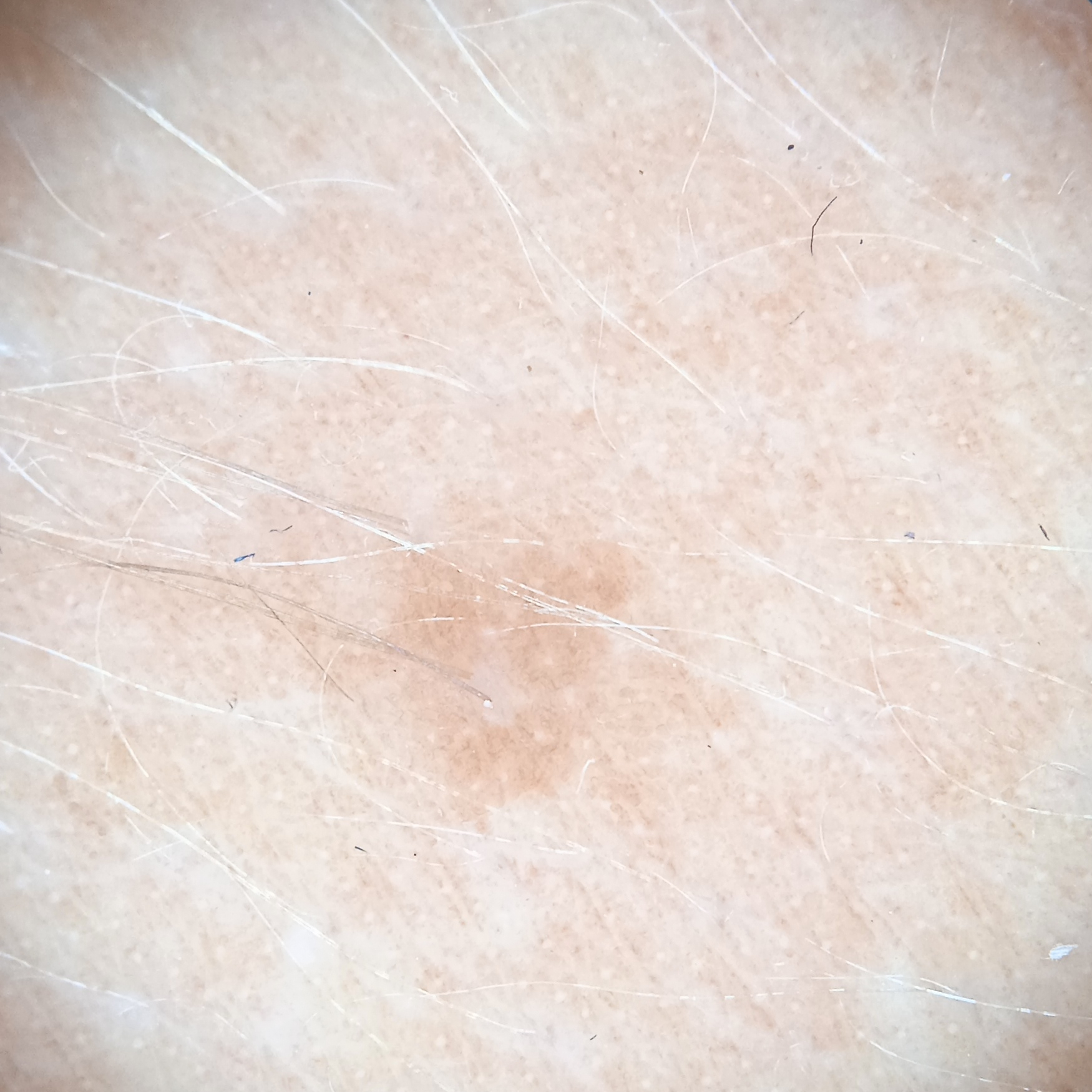The reviewing dermatologists could not reach a confident diagnosis. A moderate number of moles by the patient's own estimate.
A dermoscopy image of a skin lesion.
The patient says their skin tans without first burning.
By self-report, a history of sunbed use, no personal history of cancer, and no family history of skin cancer.
Imaged for a research study, with no referral diagnosis recorded.
A female subject 47 years old.
The lesion is located on the back.
The lesion is about 3.5 mm across.